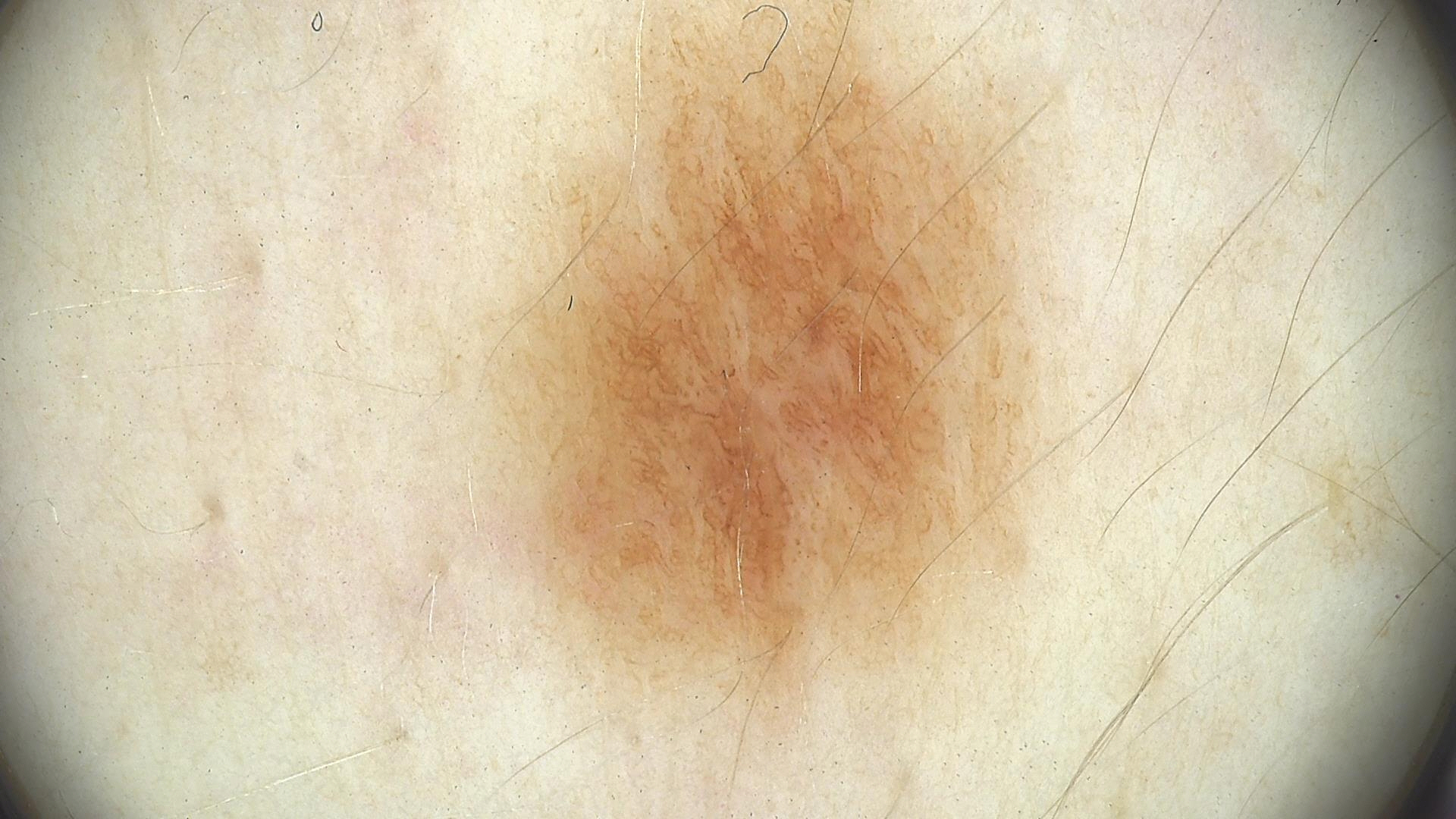A skin lesion imaged with a dermatoscope. Diagnosed as a dysplastic junctional nevus.